A male subject about 80 years old · dermoscopy of a skin lesion.
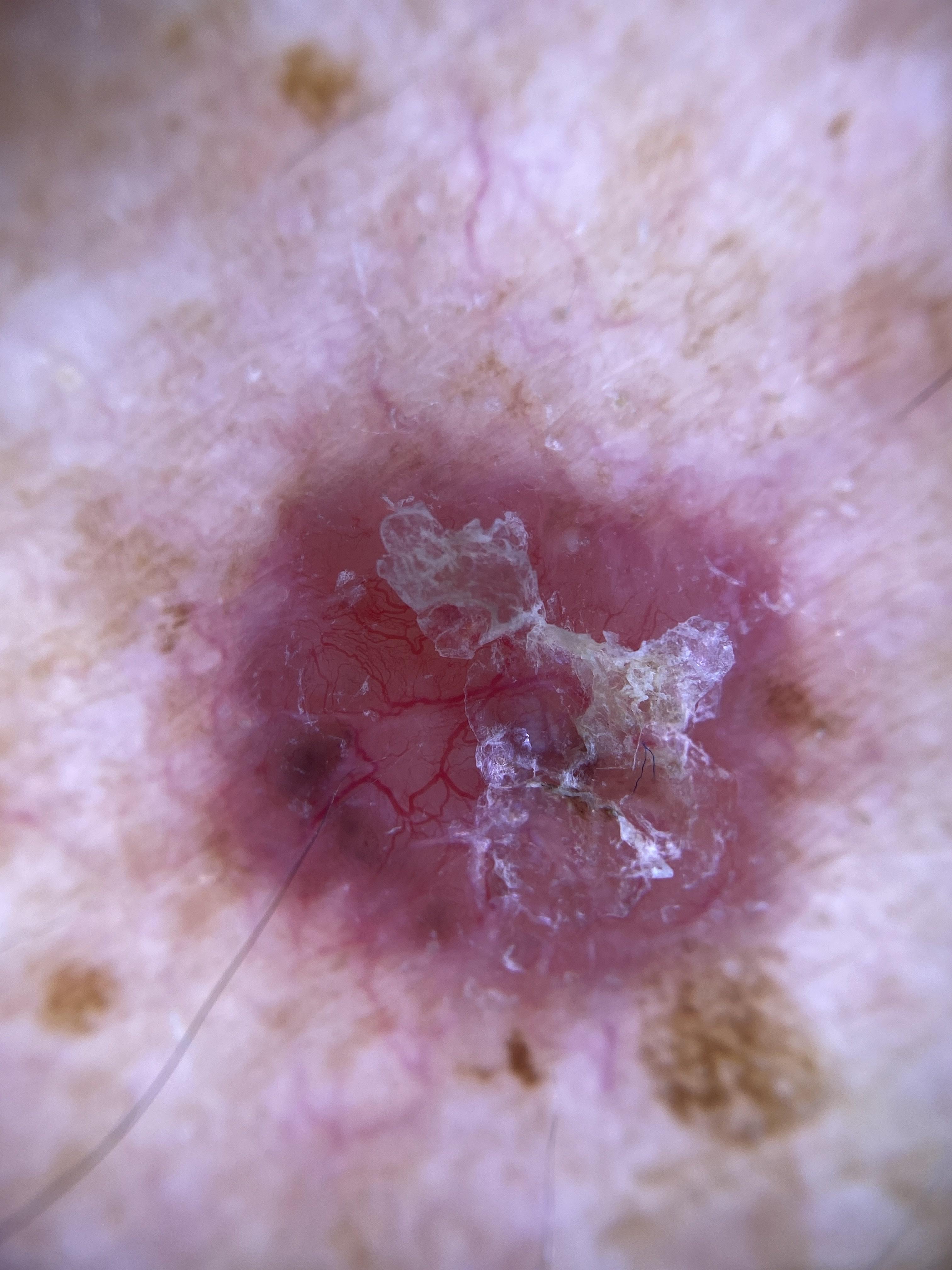Pathology:
Biopsy-confirmed as a basal cell carcinoma.